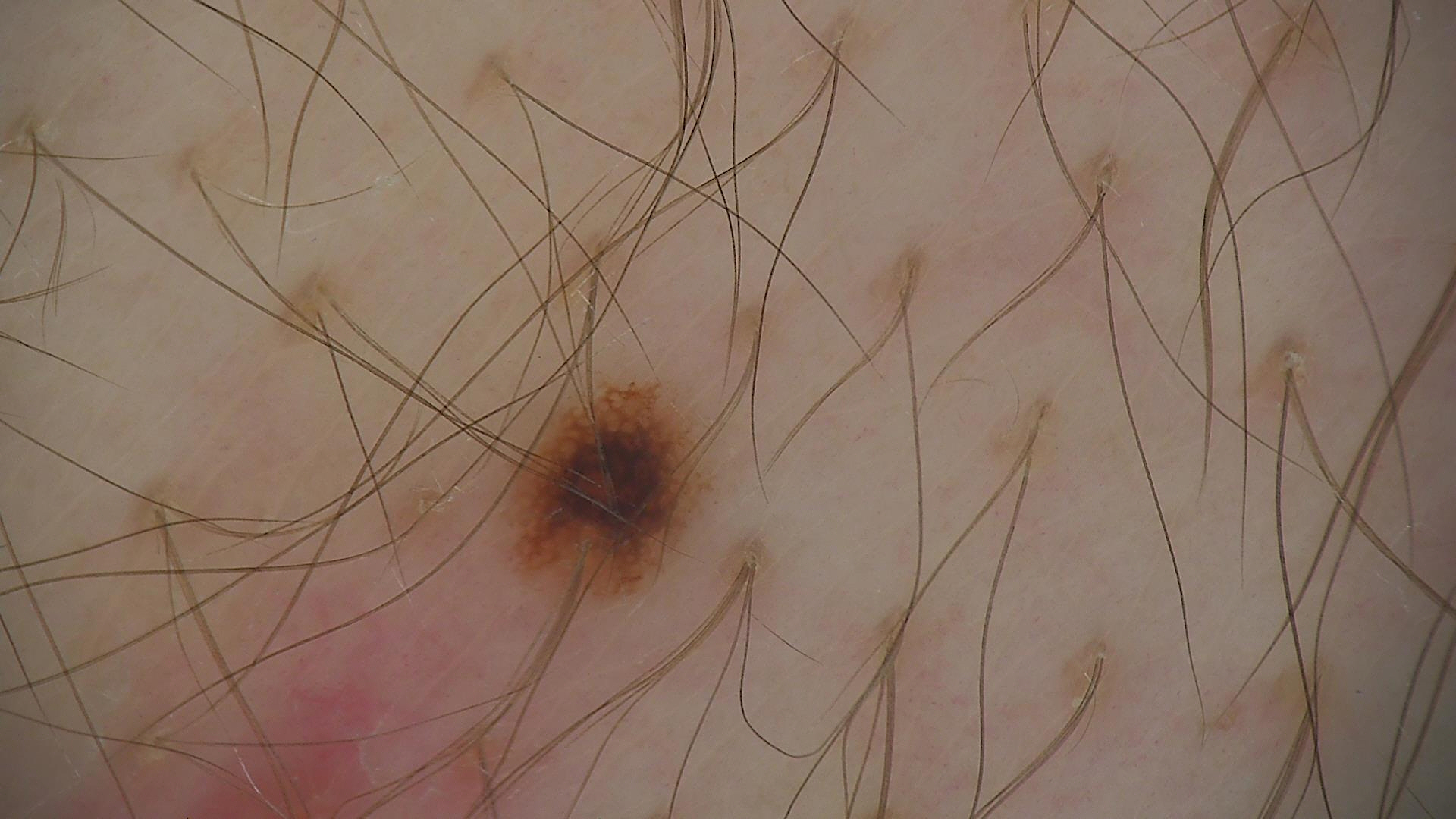{"image": "dermatoscopy", "diagnosis": {"name": "dysplastic junctional nevus", "code": "jd", "malignancy": "benign", "super_class": "melanocytic", "confirmation": "expert consensus"}}